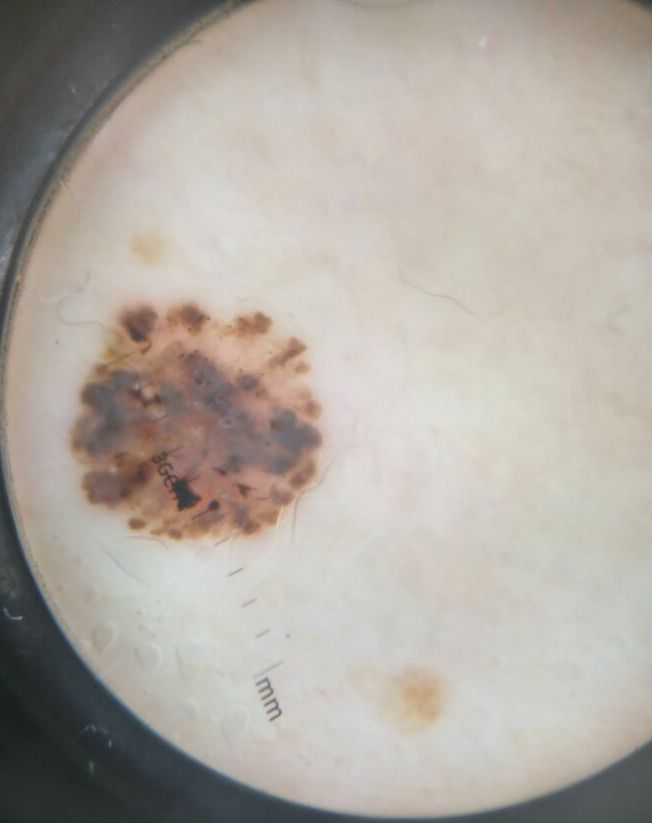A dermoscopic photograph of a skin lesion.
This is a keratinocytic lesion.
Confirmed on histopathology as a basal cell carcinoma.